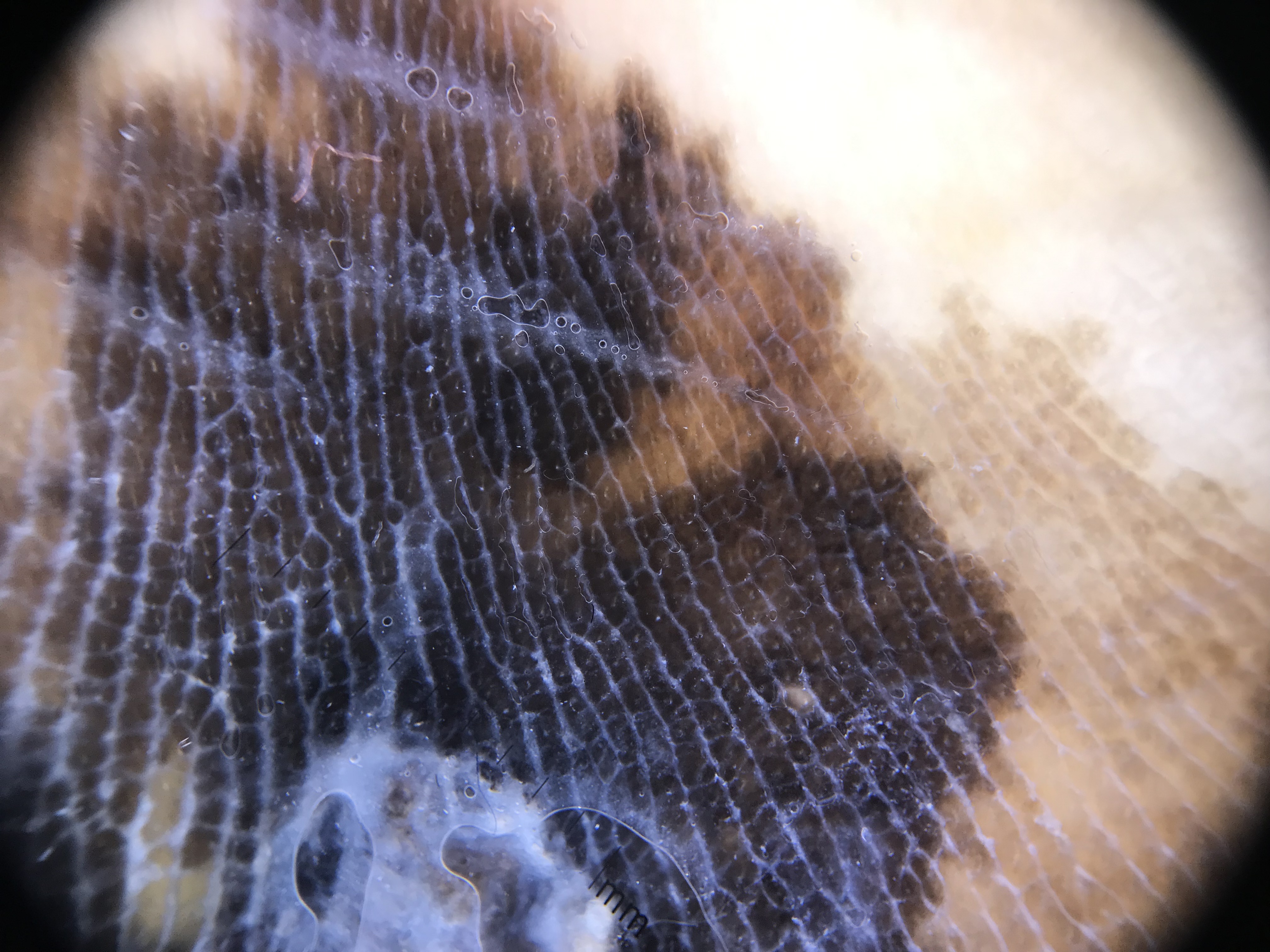<dermoscopy>
<diagnosis>
<name>acral lentiginous melanoma</name>
<code>alm</code>
<malignancy>malignant</malignancy>
<super_class>melanocytic</super_class>
<confirmation>histopathology</confirmation>
</diagnosis>
</dermoscopy>